A dermoscopic close-up of a skin lesion:
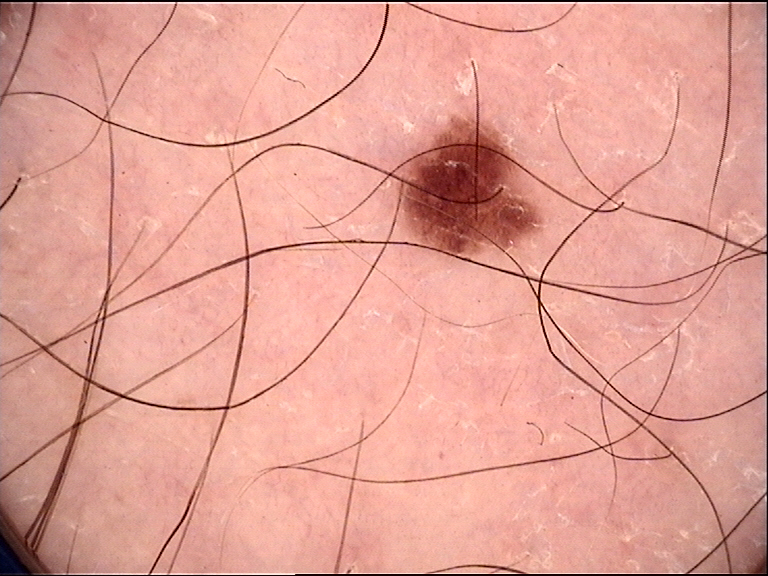Classified as a dysplastic junctional nevus.